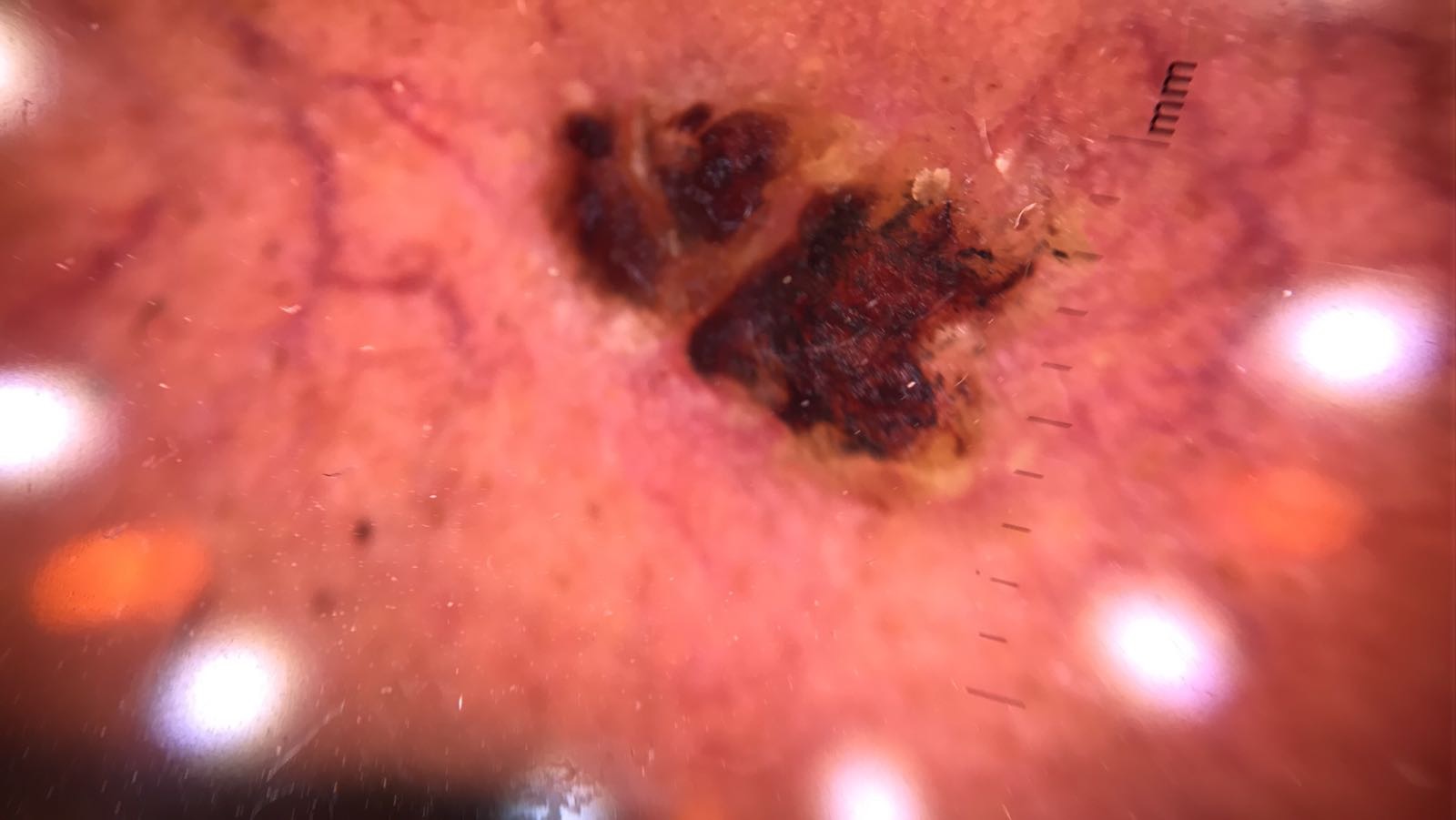Case:
* diagnosis — squamous cell carcinoma (biopsy-proven)